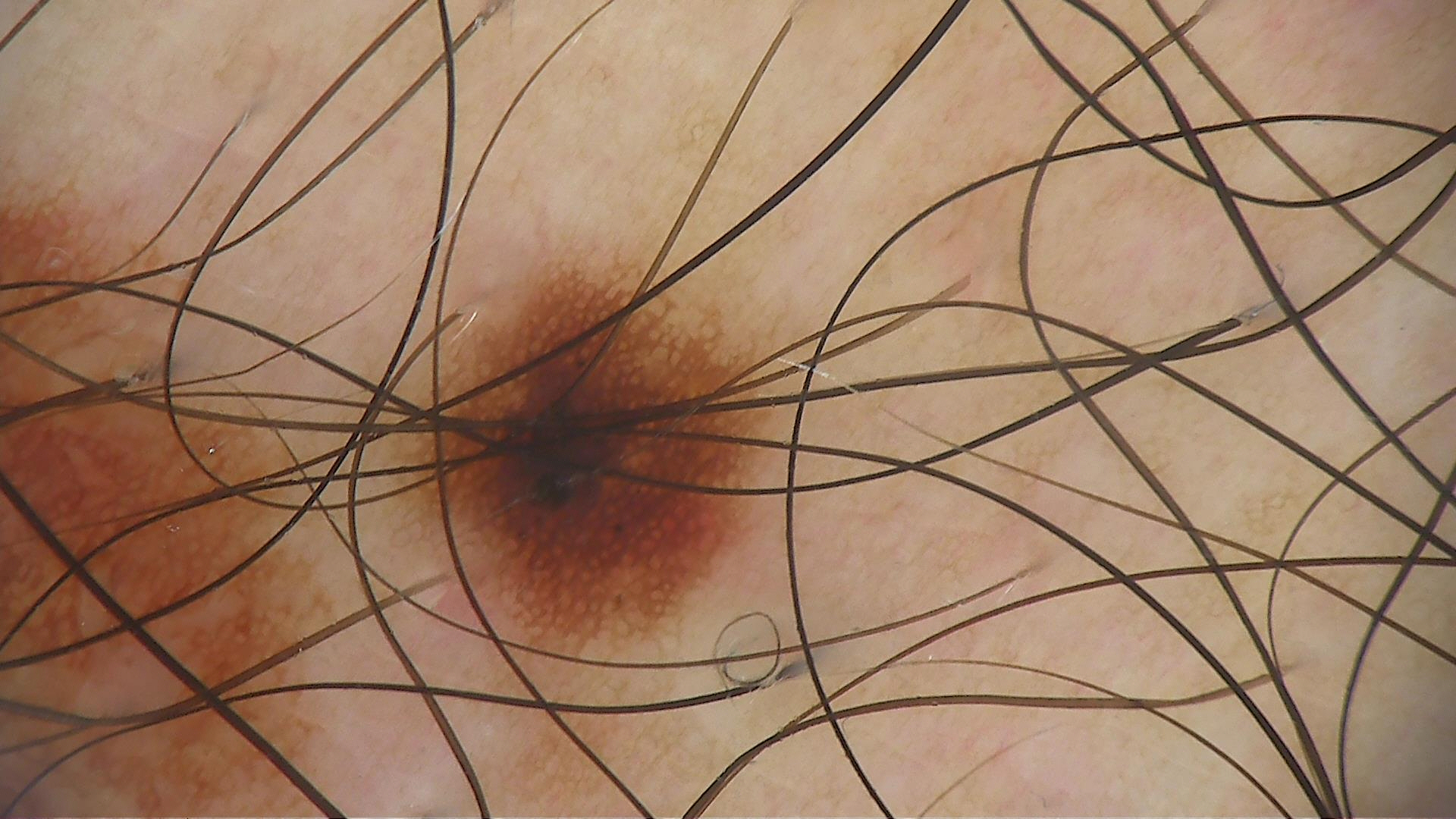class = dysplastic junctional nevus (expert consensus)